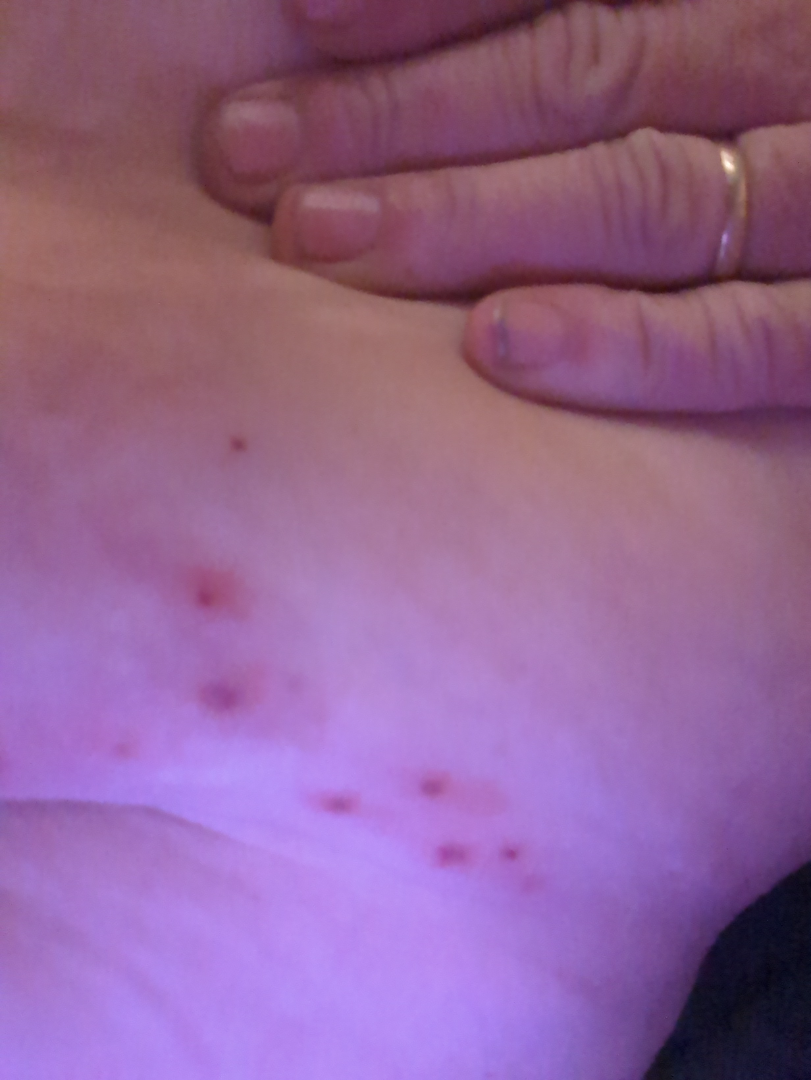Background: Texture is reported as raised or bumpy. An image taken at an angle. Present for less than one week. Reported lesion symptoms include itching. Self-categorized by the patient as a rash. Findings: On dermatologist assessment of the image, in keeping with Herpes Zoster.